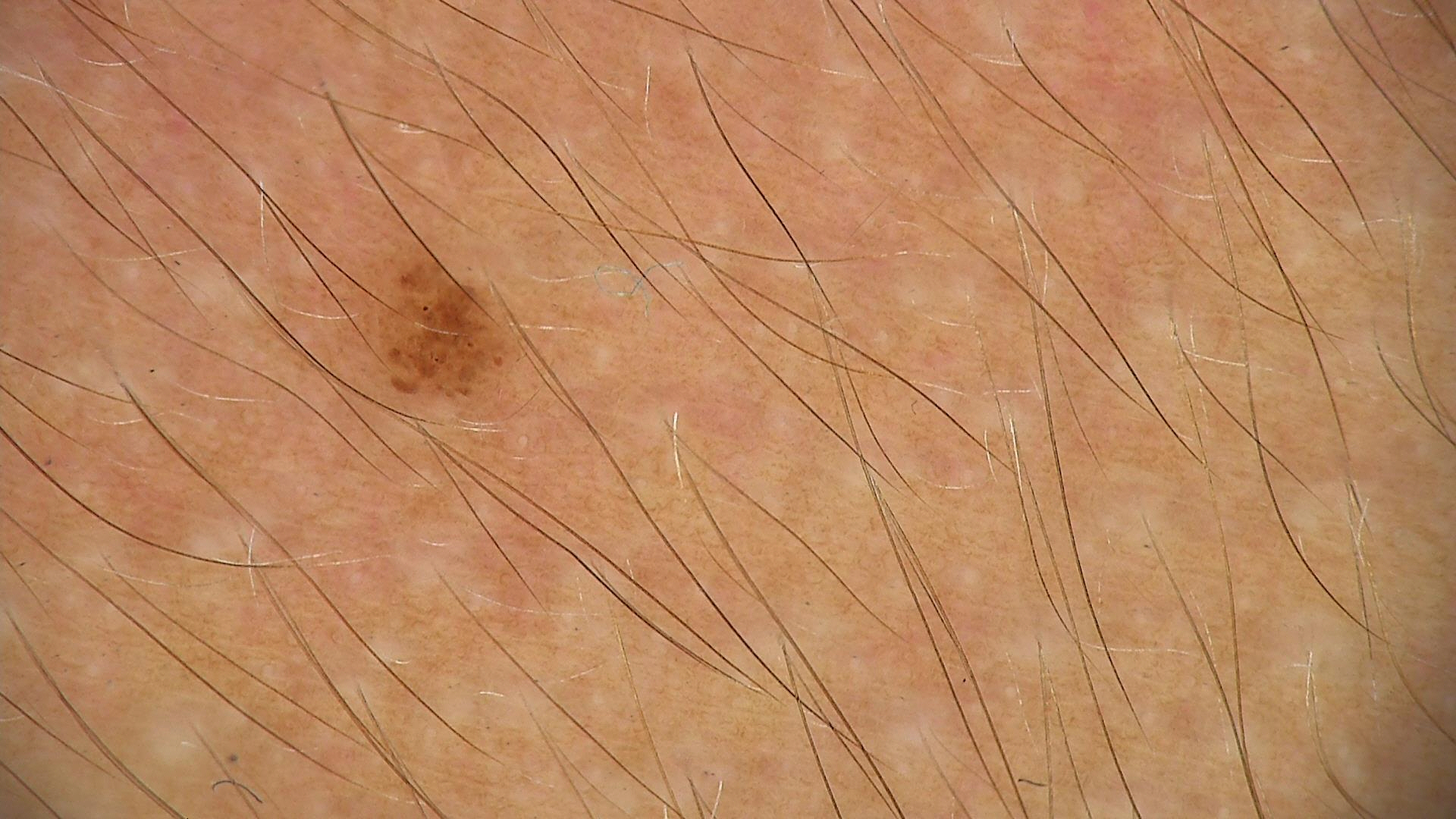diagnosis: dysplastic junctional nevus (expert consensus).